A dermatoscopic image of a skin lesion.
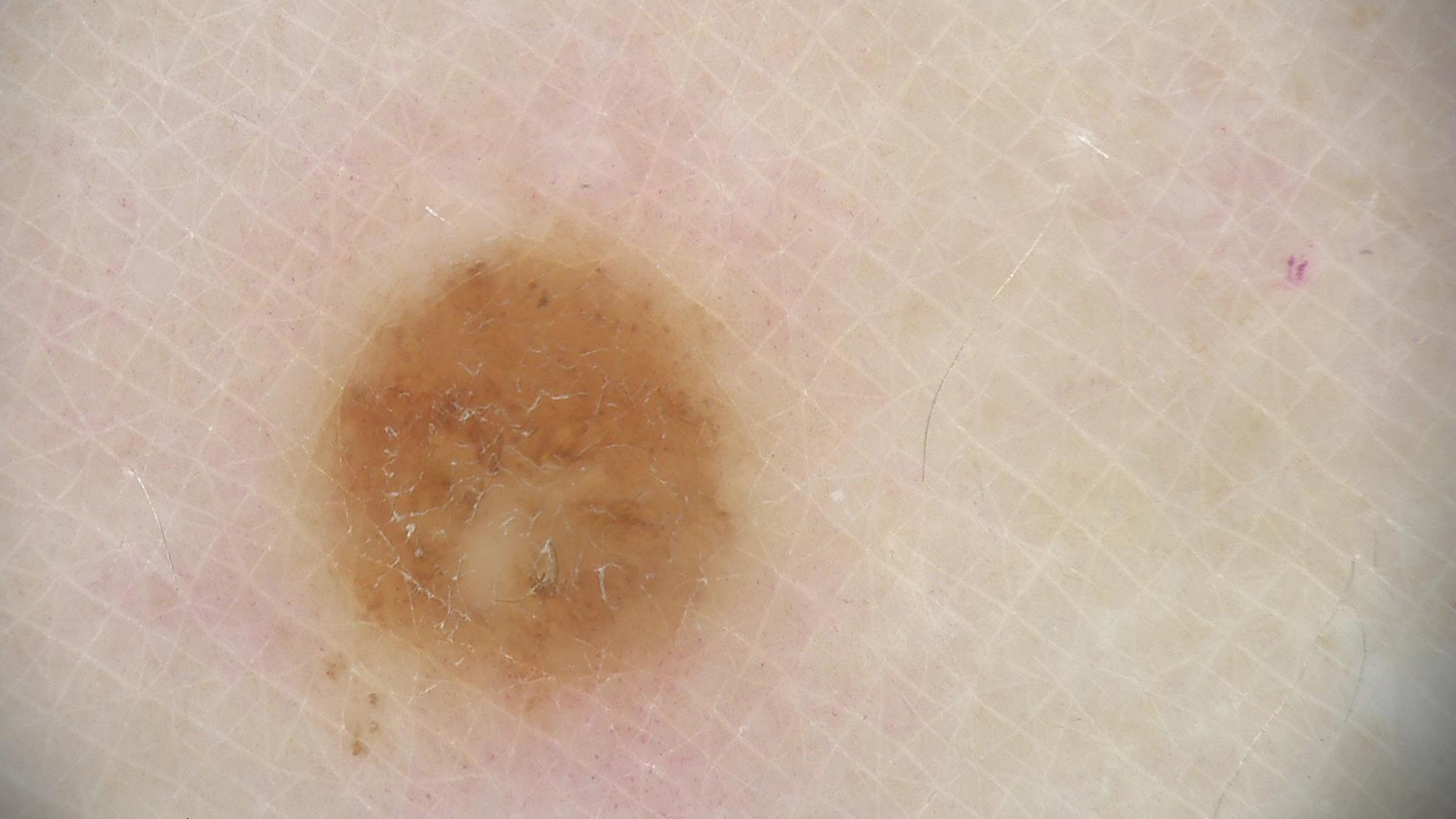label=compound nevus (expert consensus)